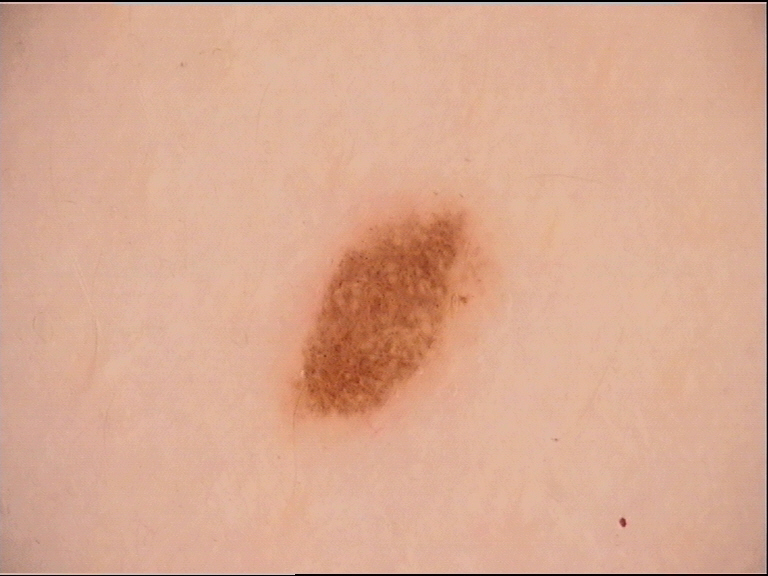image=dermoscopy | diagnostic label=dysplastic junctional nevus (expert consensus).